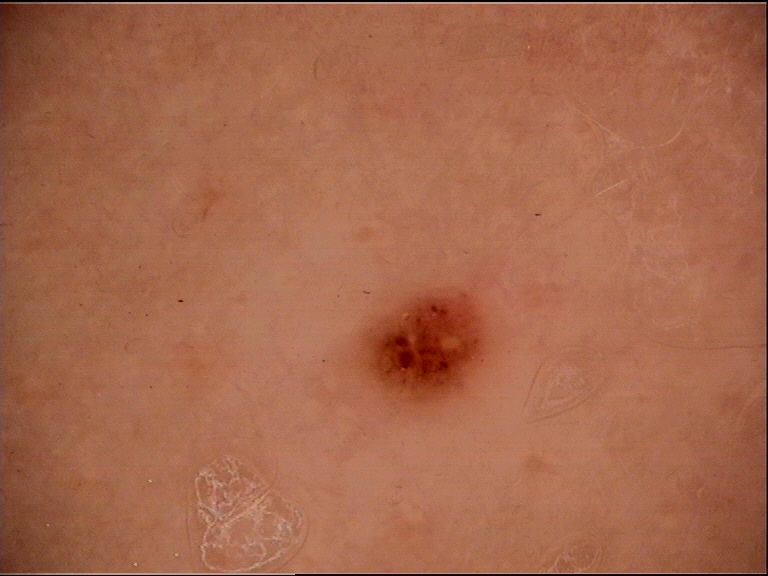A skin lesion imaged with a dermatoscope. Diagnosed as a dysplastic junctional nevus.